A dermoscopic photograph of a skin lesion.
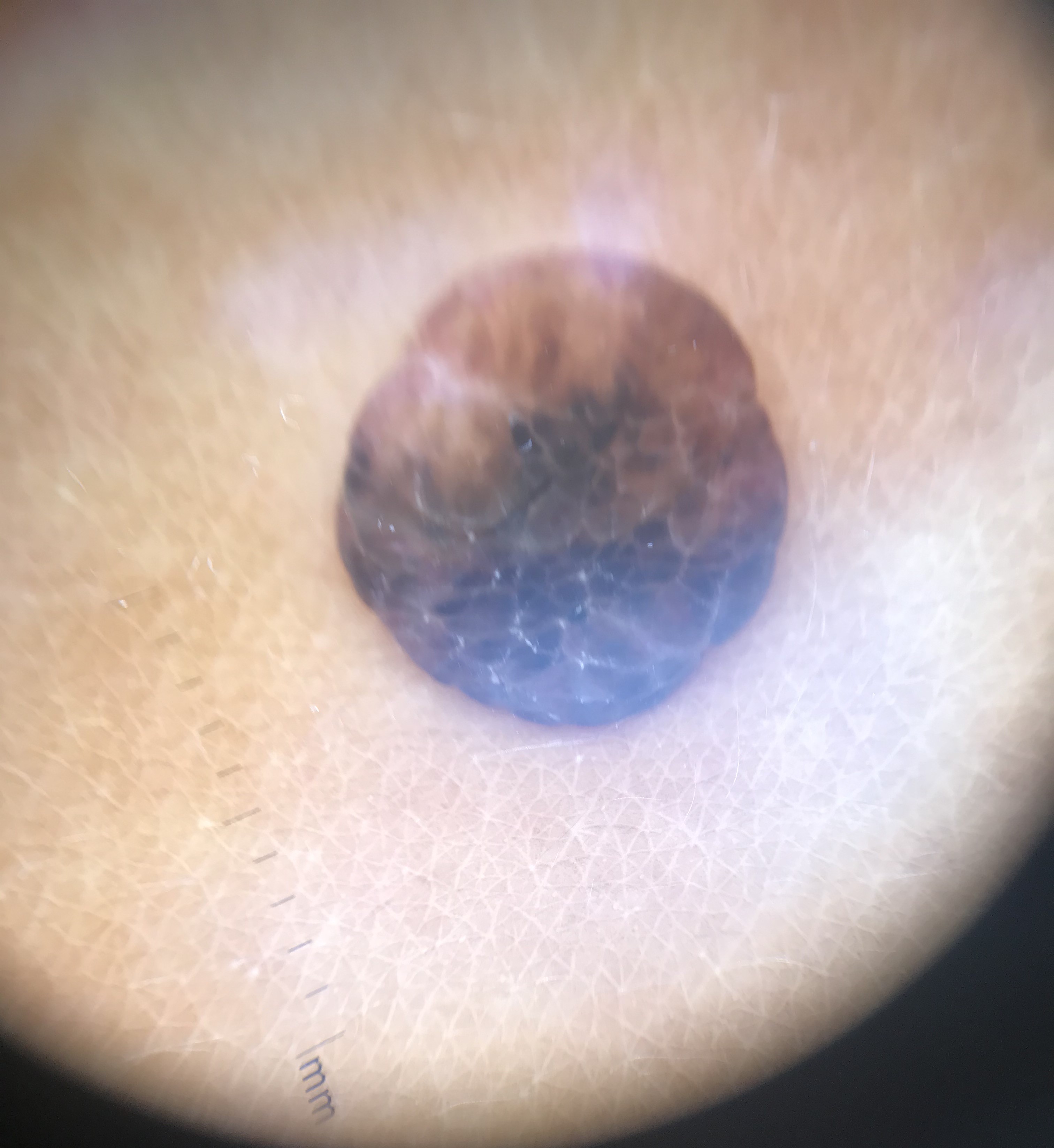Conclusion: Classified as a banal lesion — a dermal nevus.